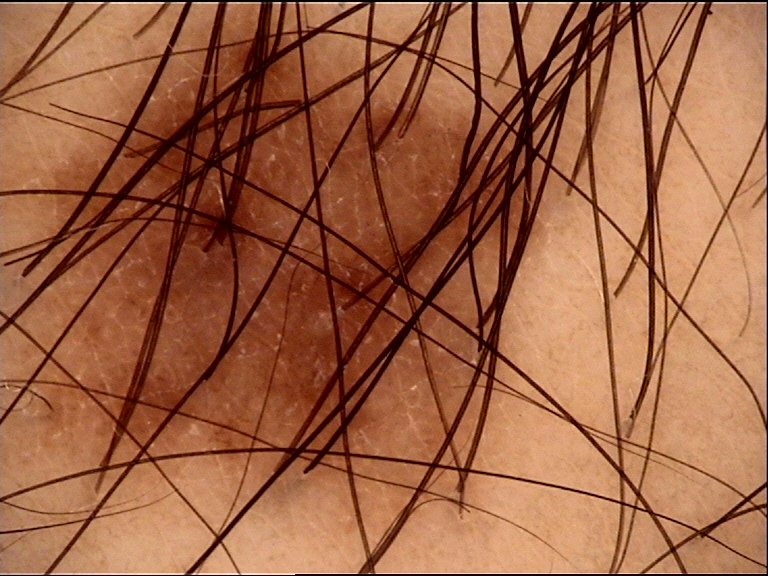Classified as a banal lesion — a junctional nevus.